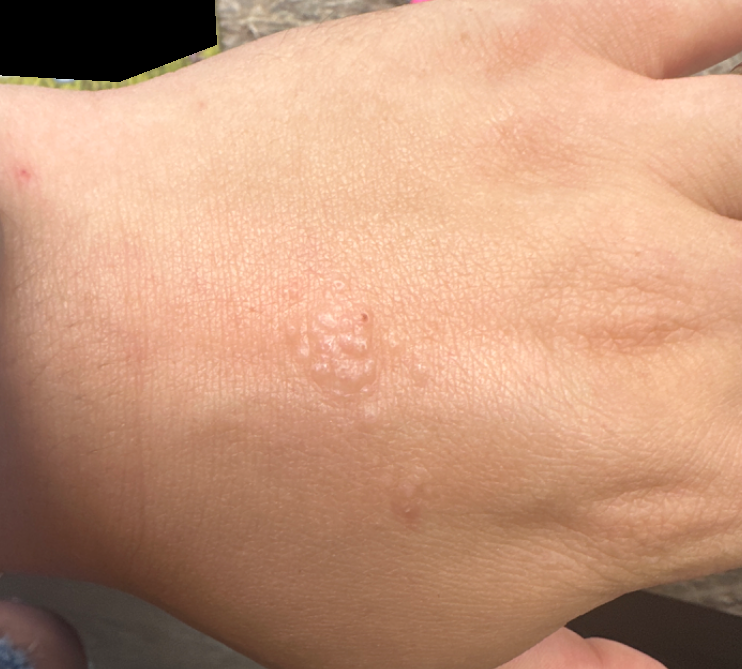The patient described the issue as a rash. Associated systemic symptoms include fatigue. Female subject, age 18–29. The lesion involves the back of the hand. The lesion is associated with itching, enlargement, bothersome appearance and pain. Close-up view. The lesion is described as fluid-filled and raised or bumpy. Present for one to four weeks. On photographic review, the primary impression is Contact dermatitis; with consideration of Lichen nitidus; possibly Eczema; also raised was Allergic Contact Dermatitis.